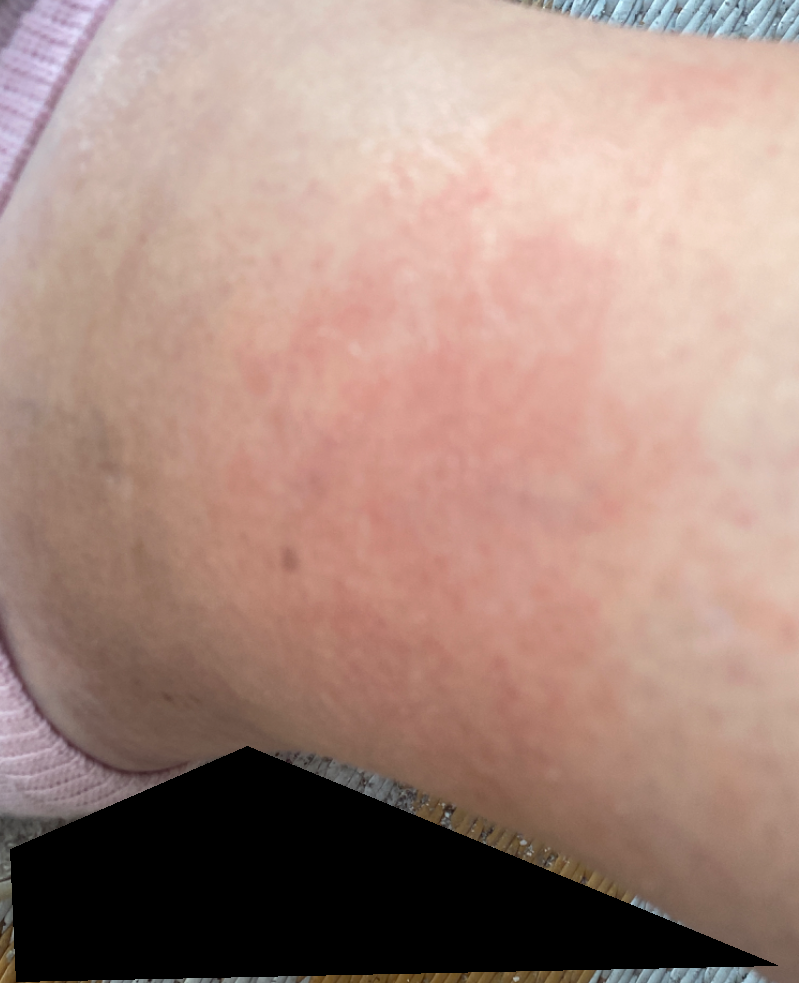Background:
This is a close-up image.
Findings:
Consistent with Eczema.